Recorded as Fitzpatrick I — 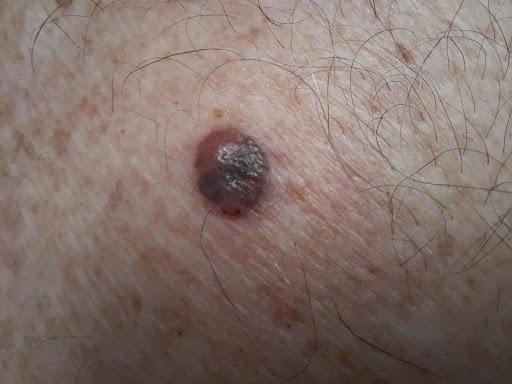Q: Where is the lesion located?
A: the trunk, specifically the posterior trunk
Q: What did the workup show?
A: Melanoma (biopsy-proven)